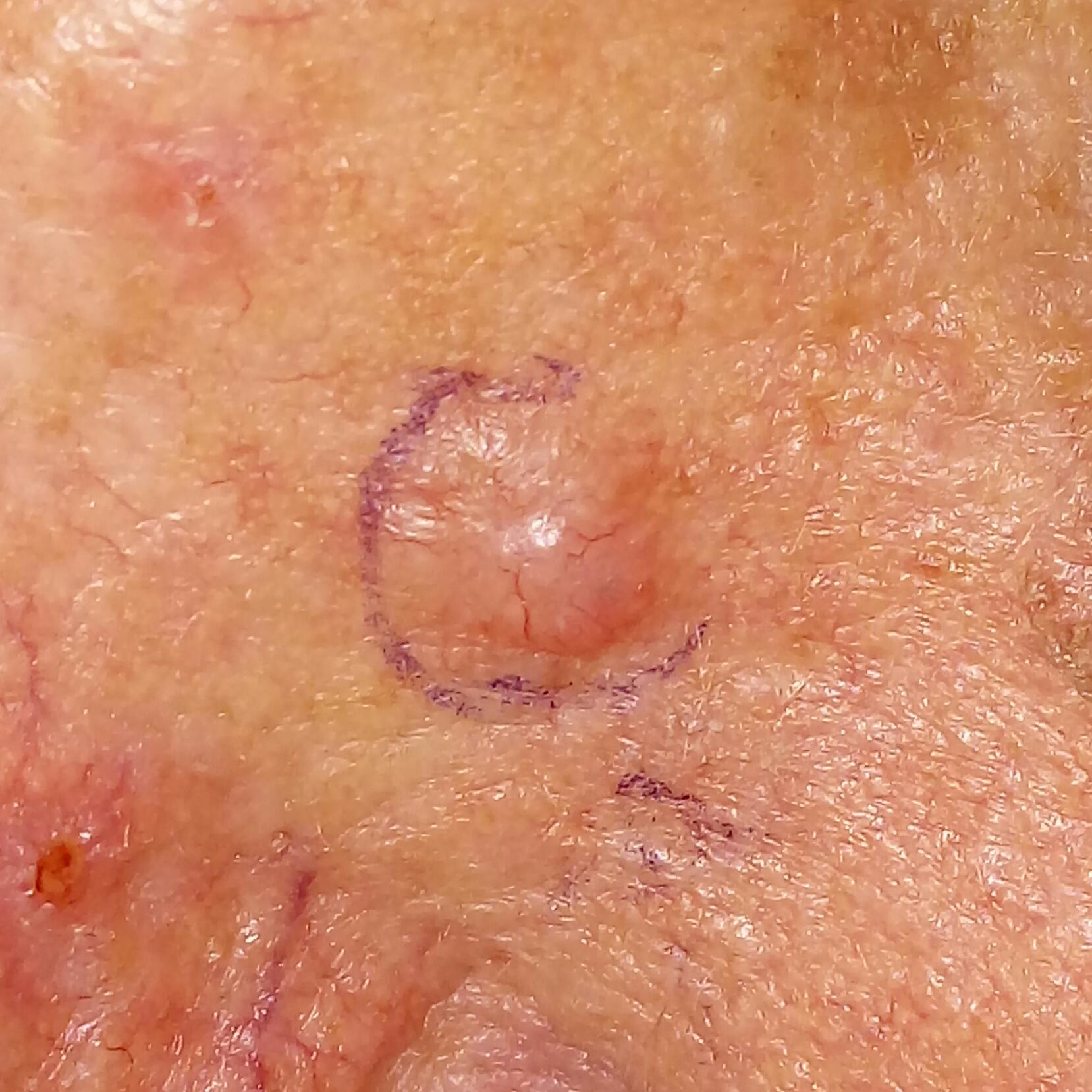The patient is skin type II. A smartphone photograph of a skin lesion. A male subject in their early 70s. Located on the nose. Measuring about 7 × 5 mm. The patient describes that the lesion is elevated. Biopsy-confirmed as a malignant lesion — a basal cell carcinoma.